The lesion involves the front of the torso, the contributor is a male aged 50–59, the photograph is a close-up of the affected area, reported duration is one to four weeks, the patient notes itching, texture is reported as flat, self-categorized by the patient as a rash.
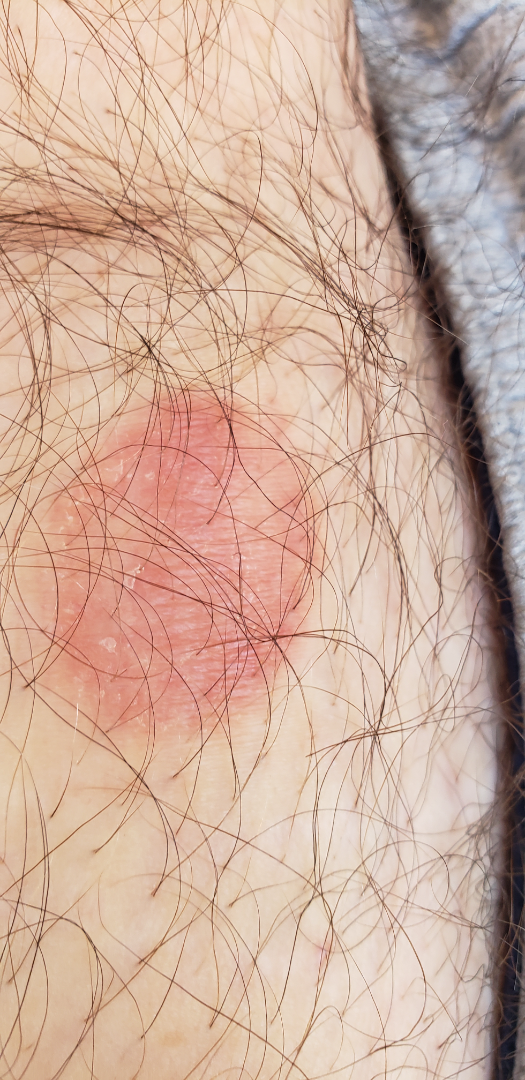dermatologist impression — Melanocytic Nevus (weight 0.54); Actinic Keratosis (weight 0.23); Atypical Nevus (weight 0.23)